The condition has been present for one to four weeks; texture is reported as fluid-filled; the patient described the issue as a rash; symptoms reported: itching, burning, bleeding, enlargement, darkening and pain; close-up view; the back of the hand is involved; the patient is 30–39, female:
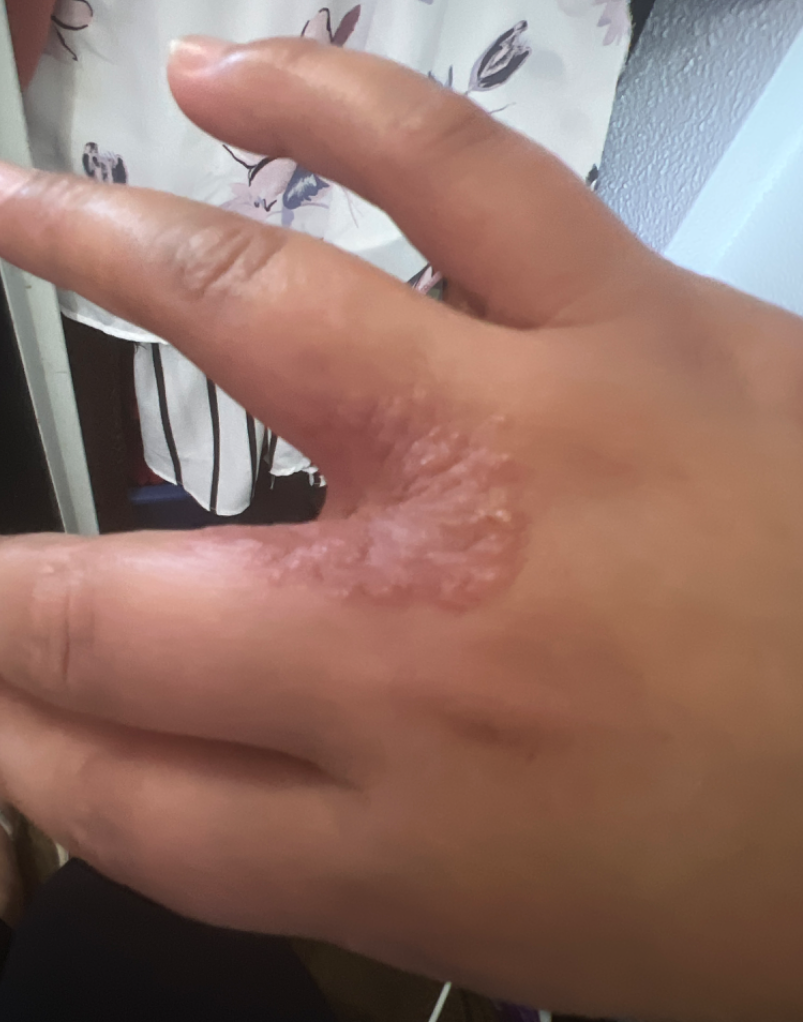On remote review of the image: Candida and Eczema were each considered, in no particular order; a remote consideration is Tinea; lower on the differential is Psoriasis.